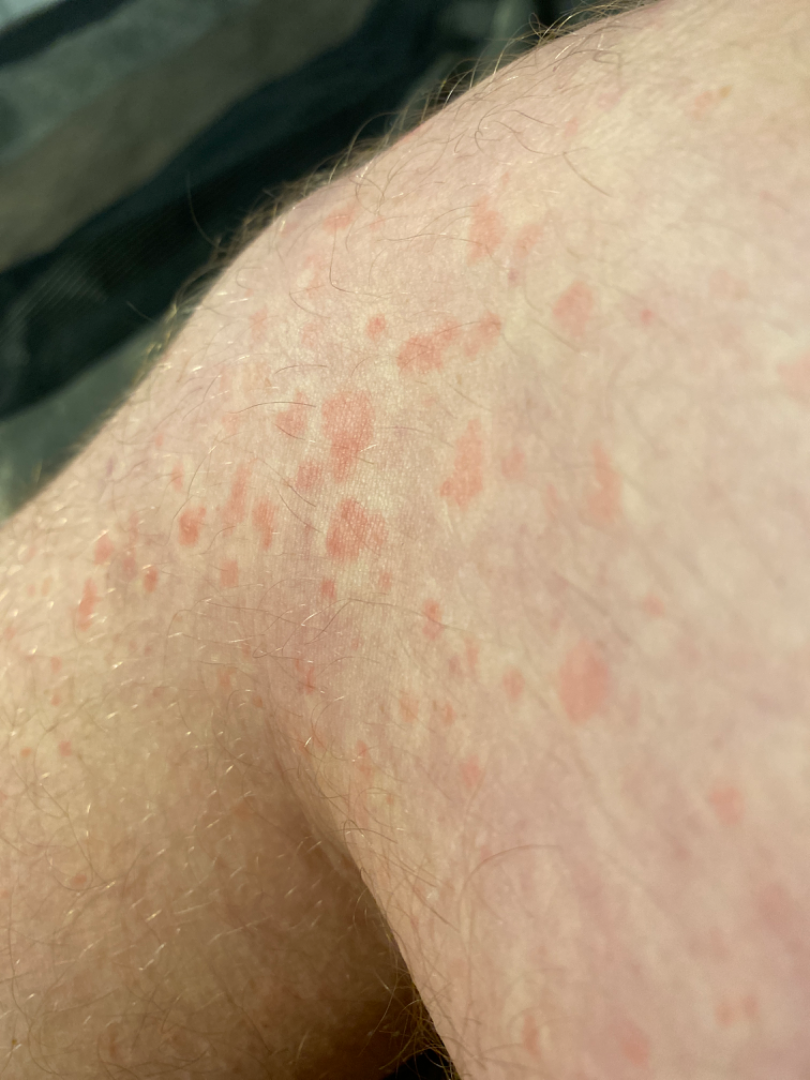Reported lesion symptoms include itching and bothersome appearance.
Reported duration is less than one week.
Located on the leg.
The photo was captured at an angle.
The patient notes the lesion is raised or bumpy.
The favored diagnosis is Urticaria; also consider Leukocytoclastic Vasculitis.